The affected area is the front of the torso and back of the torso. The subject is 18–29, female. The photo was captured at an angle — 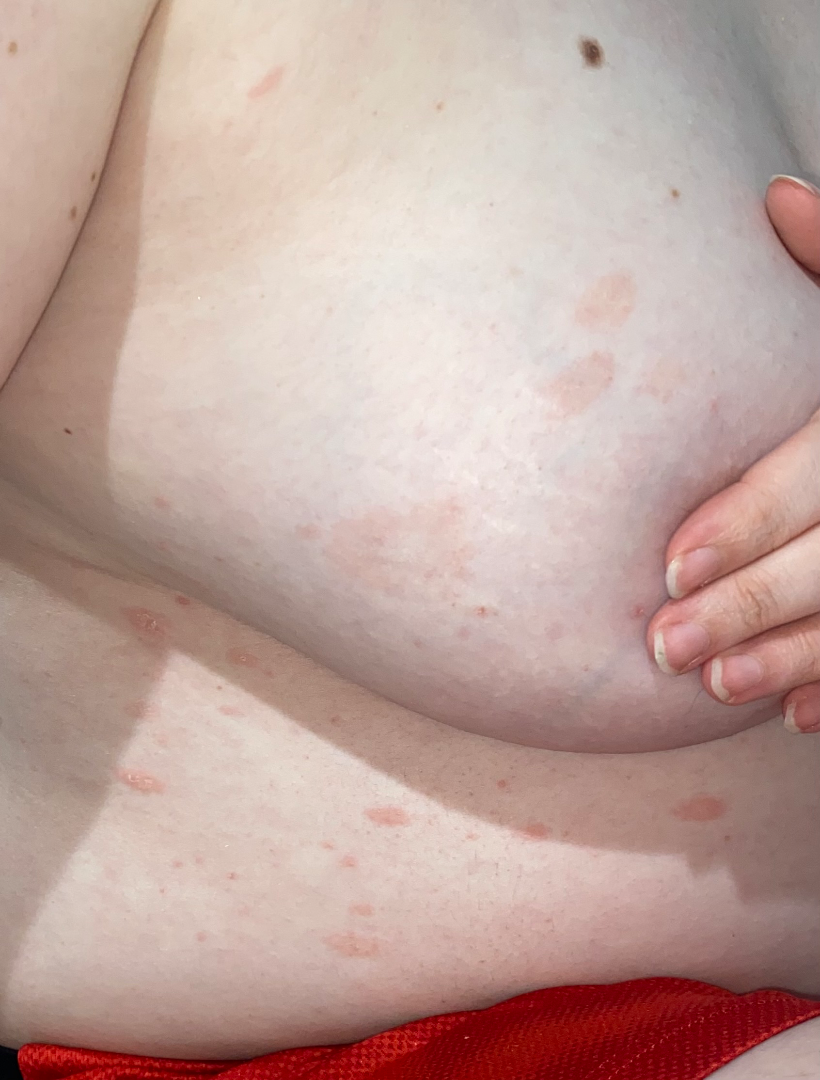History: The lesion is described as raised or bumpy and rough or flaky. The contributor notes bothersome appearance and enlargement. The condition has been present for one to four weeks. Impression: The leading consideration is Pityriasis rosea; also raised was Psoriasis; less probable is Eczema.